The patient is a female in their mid- to late 40s · a skin lesion imaged with a dermatoscope: 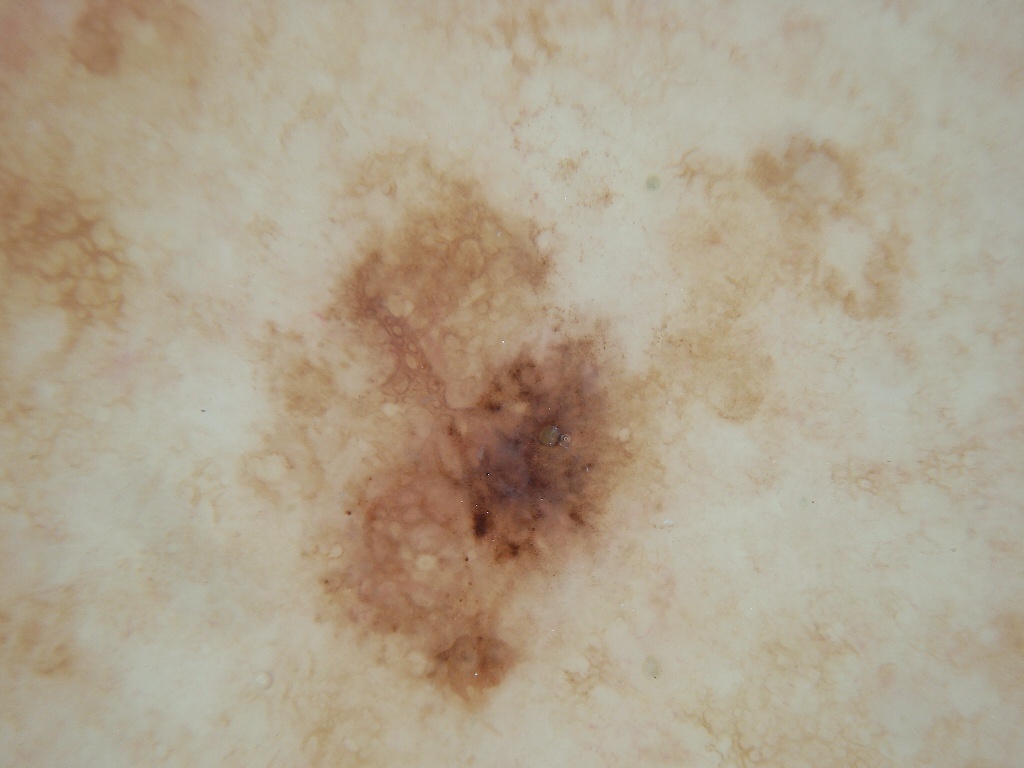{
  "lesion_extent": "moderate",
  "dermoscopic_features": {
    "present": [
      "pigment network"
    ],
    "absent": [
      "globules",
      "streaks",
      "milia-like cysts",
      "negative network"
    ]
  },
  "lesion_location": {
    "bbox_xyxy": [
      283,
      174,
      650,
      717
    ]
  },
  "diagnosis": {
    "name": "melanoma",
    "malignancy": "malignant",
    "lineage": "melanocytic",
    "provenance": "histopathology"
  }
}